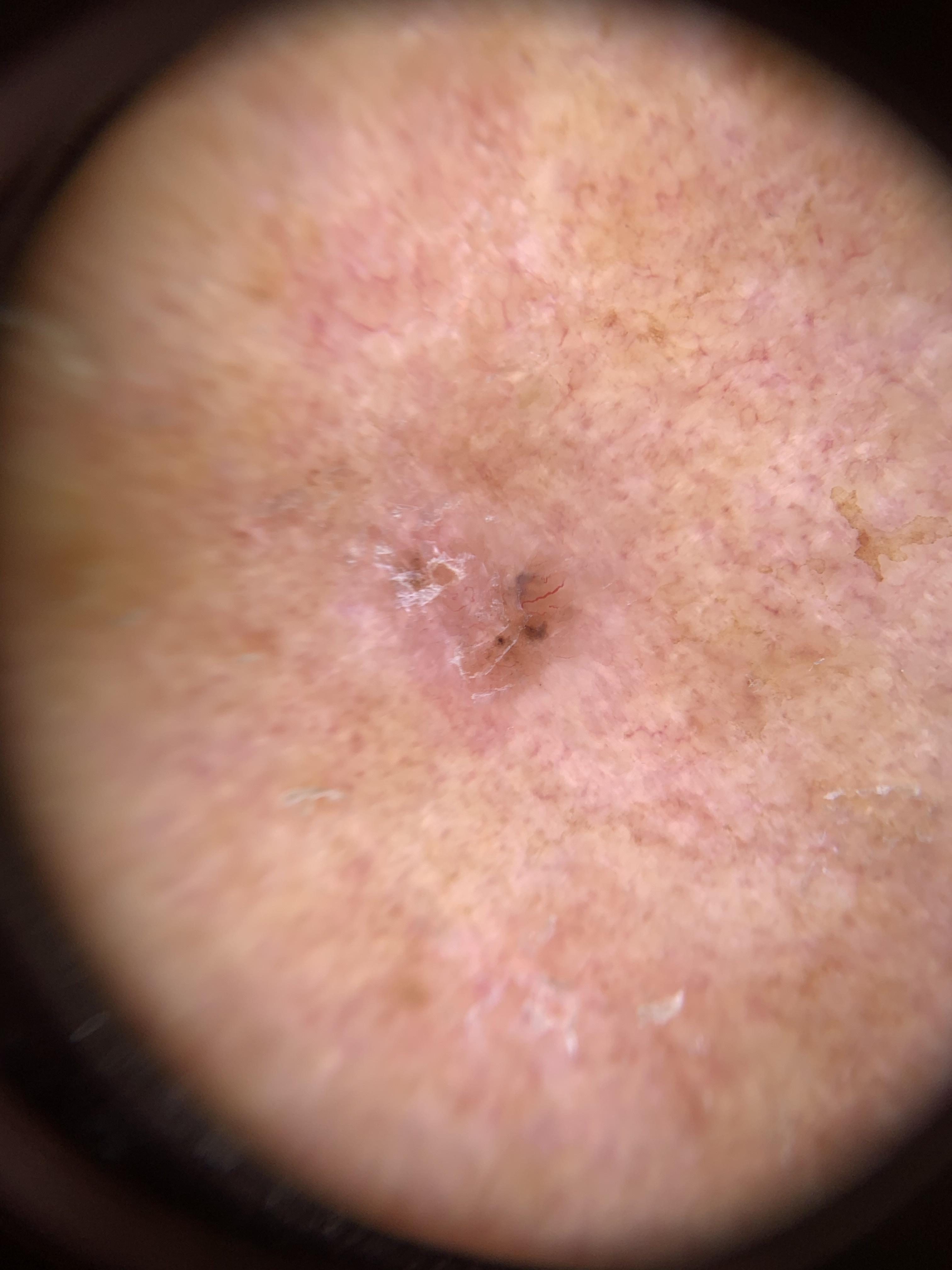Findings: A skin lesion imaged with a dermatoscope. A male subject approximately 75 years of age. Recorded as Fitzpatrick phototype II. Located on the head or neck. Conclusion: Histopathology confirmed a basal cell carcinoma.